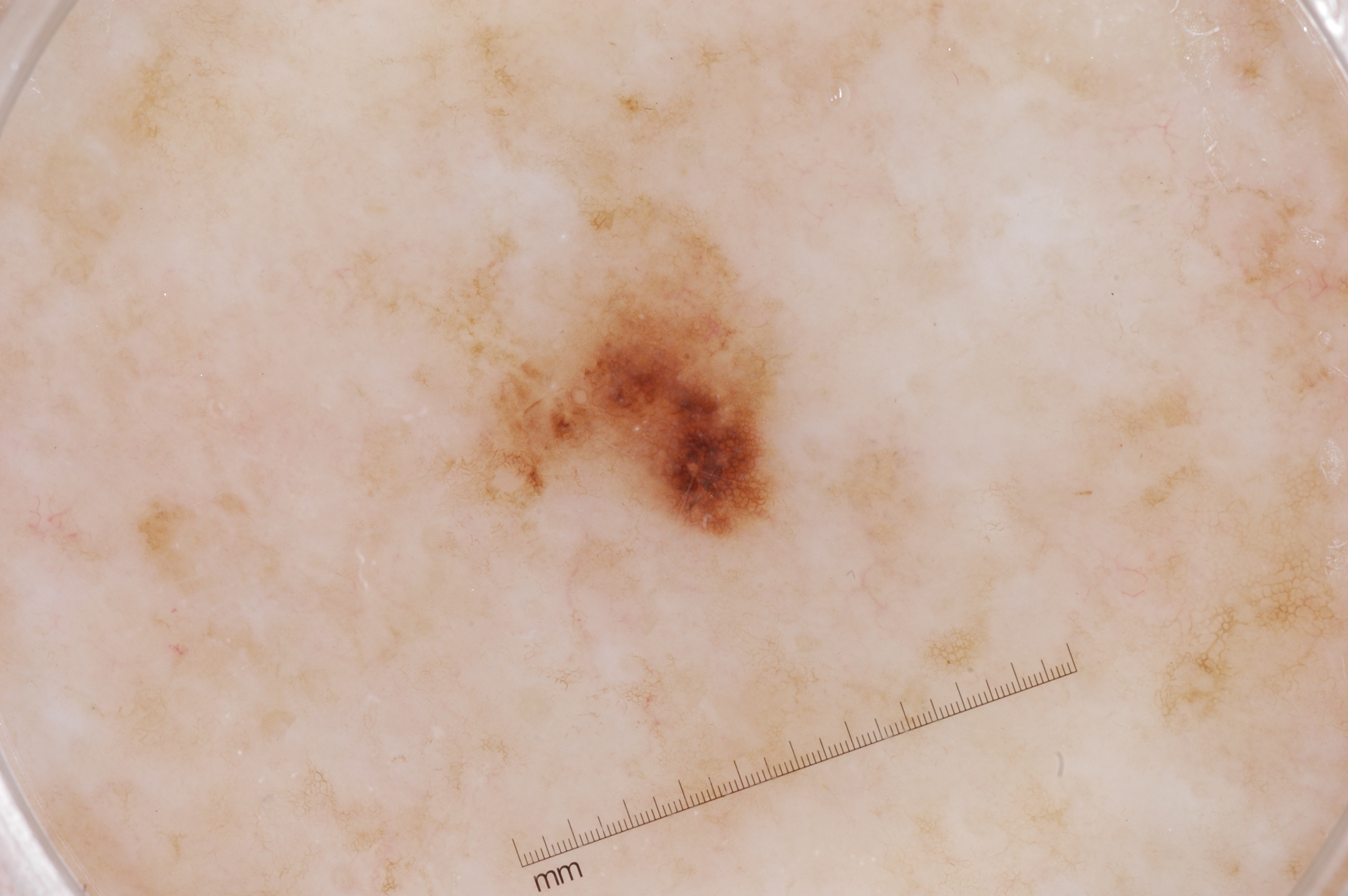subject = female, aged around 70
modality = dermatoscopic image of a skin lesion
features = milia-like cysts and pigment network; absent: negative network and streaks
lesion bbox = x1=474, y1=217, x2=779, y2=539
extent = ~5% of the field
diagnosis = a melanoma